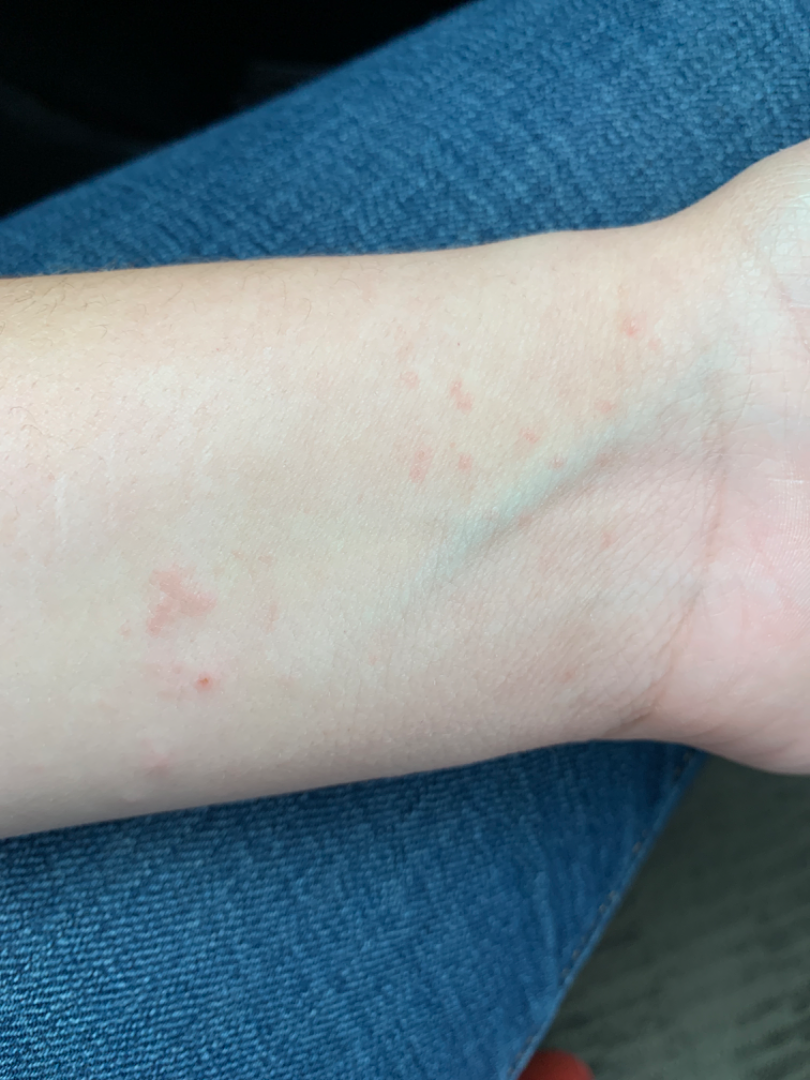The contributor reports the lesion is raised or bumpy.
Close-up view.
The patient described the issue as a rash.
Symptoms reported: itching.
Located on the arm.
No associated systemic symptoms reported.
On remote review of the image: Allergic Contact Dermatitis (54%); Lichen planus/lichenoid eruption (23%); Eczema (23%).